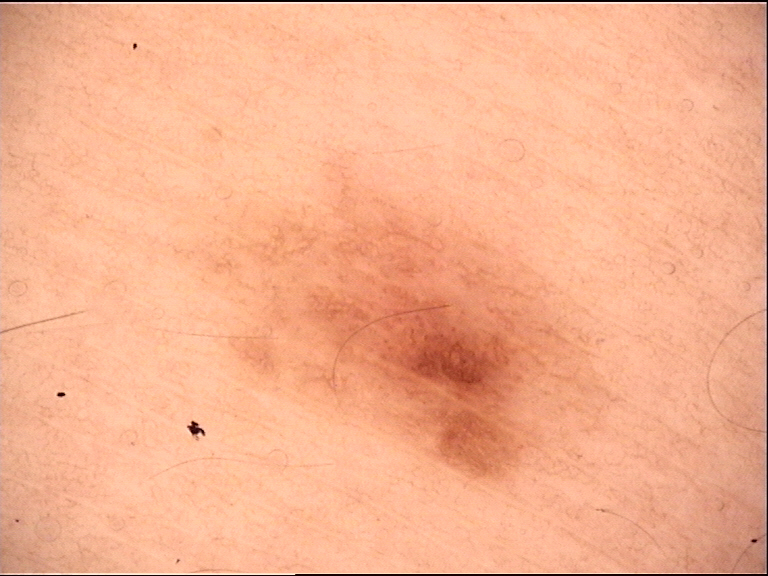The morphology is that of a banal lesion.
Consistent with a junctional nevus.